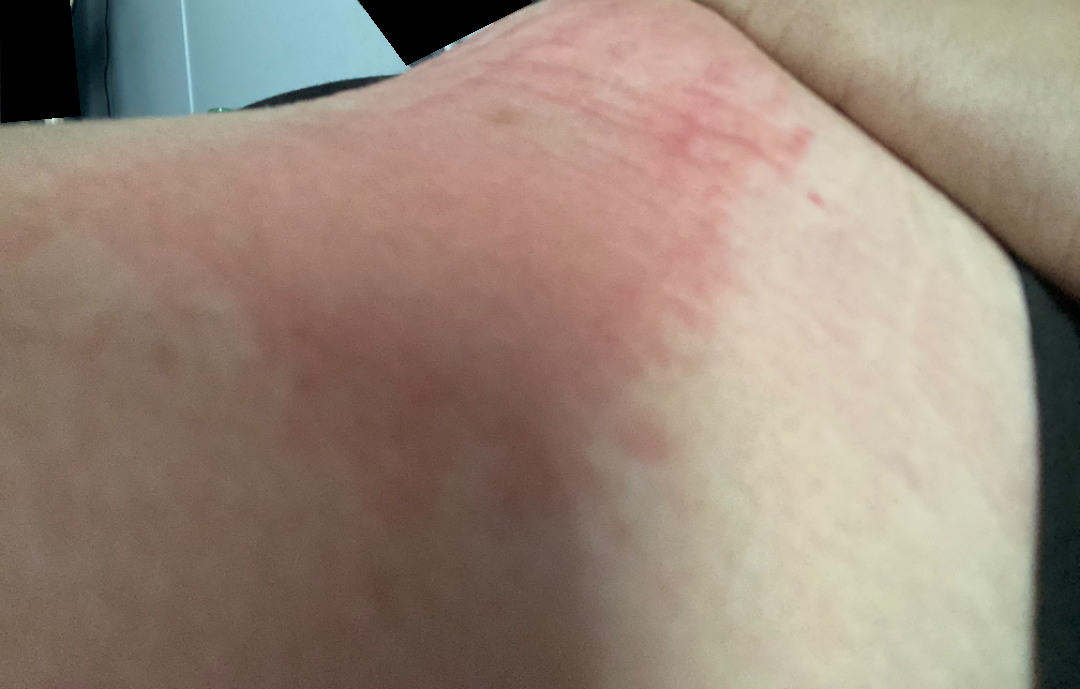| field | value |
|---|---|
| patient-reported symptoms | darkening, enlargement, burning, bothersome appearance and itching |
| described texture | raised or bumpy |
| contributor | female, age 18–29 |
| constitutional symptoms | none reported |
| onset | less than one week |
| self-categorized as | skin that appeared healthy to them |
| location | front of the torso |
| view | at an angle |
| assessment | the leading impression is Allergic Contact Dermatitis; lower on the differential is Acute dermatitis, NOS; less probable is Cellulitis; a remote consideration is Tinea; less likely is Eczema; a more distant consideration is Urticarial vasculitis |